Dermoscopy of a skin lesion: 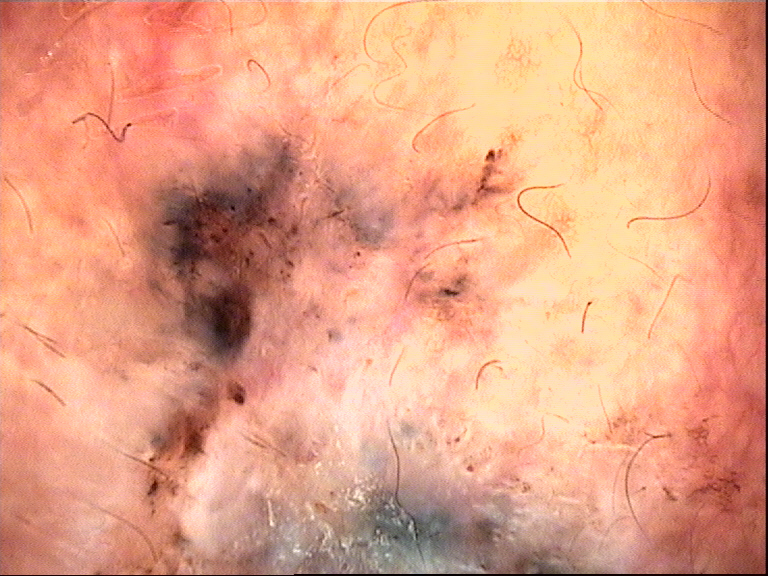Conclusion: Confirmed on histopathology as a malignant, keratinocytic lesion — a basal cell carcinoma.